Collected as part of a research study, without a referral diagnosis — 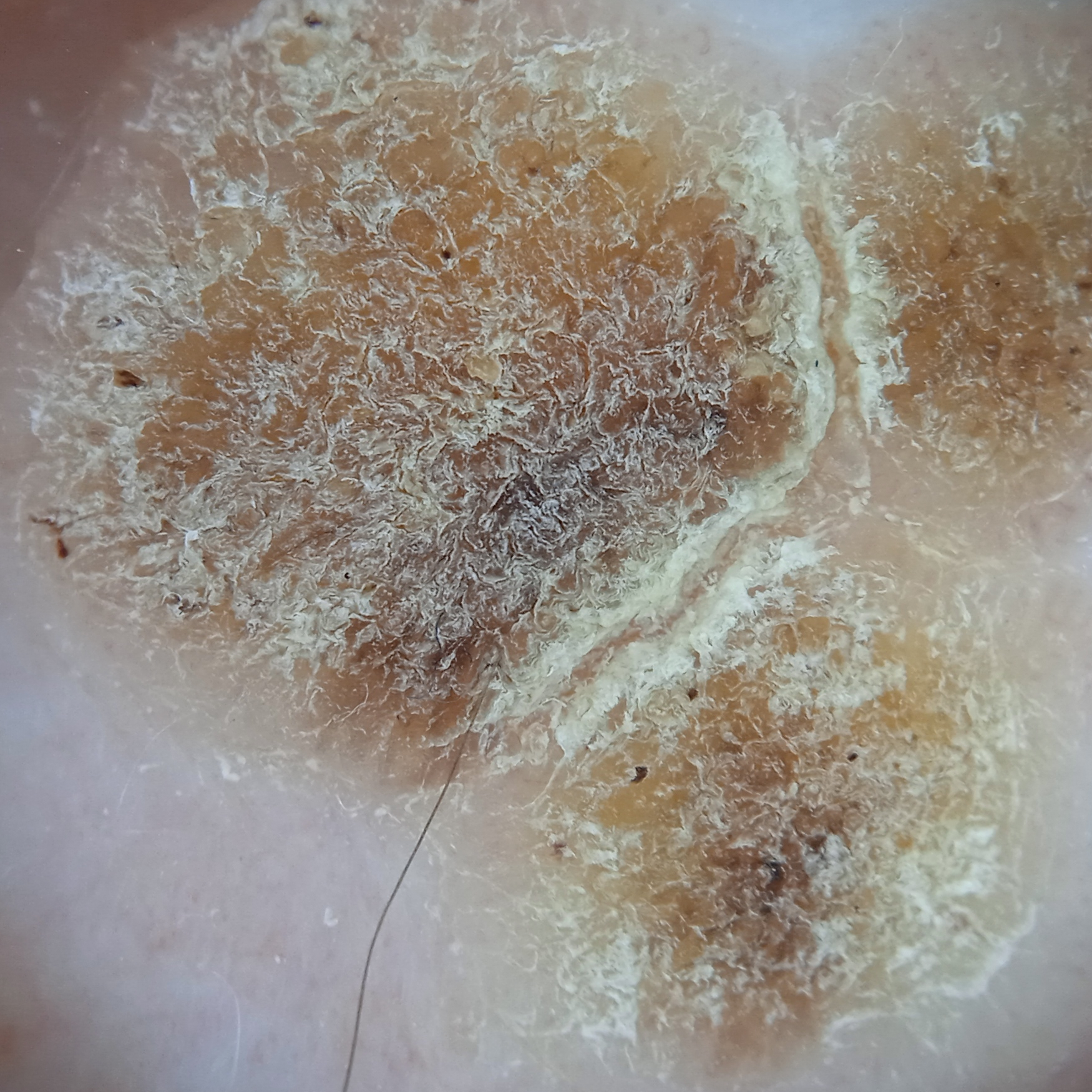The lesion is located on the back. The lesion measures approximately 14.2 mm. The diagnostic impression was a seborrheic keratosis.